A female patient in their mid-60s. History notes prior malignancy (patient or family), prior skin cancer (patient or family), and no pesticide exposure. The patient was assessed as Fitzpatrick phototype II. A smartphone photograph of a skin lesion: 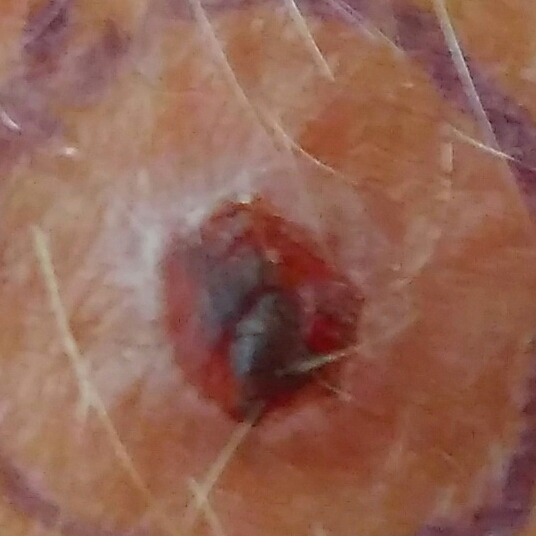Q: Where on the body is the lesion?
A: a forearm
Q: What did the workup show?
A: basal cell carcinoma (biopsy-proven)